Fitzpatrick skin type V; lay reviewers estimated Monk skin tone scale 8 (US pool) or 7 (India pool). This image was taken at an angle: 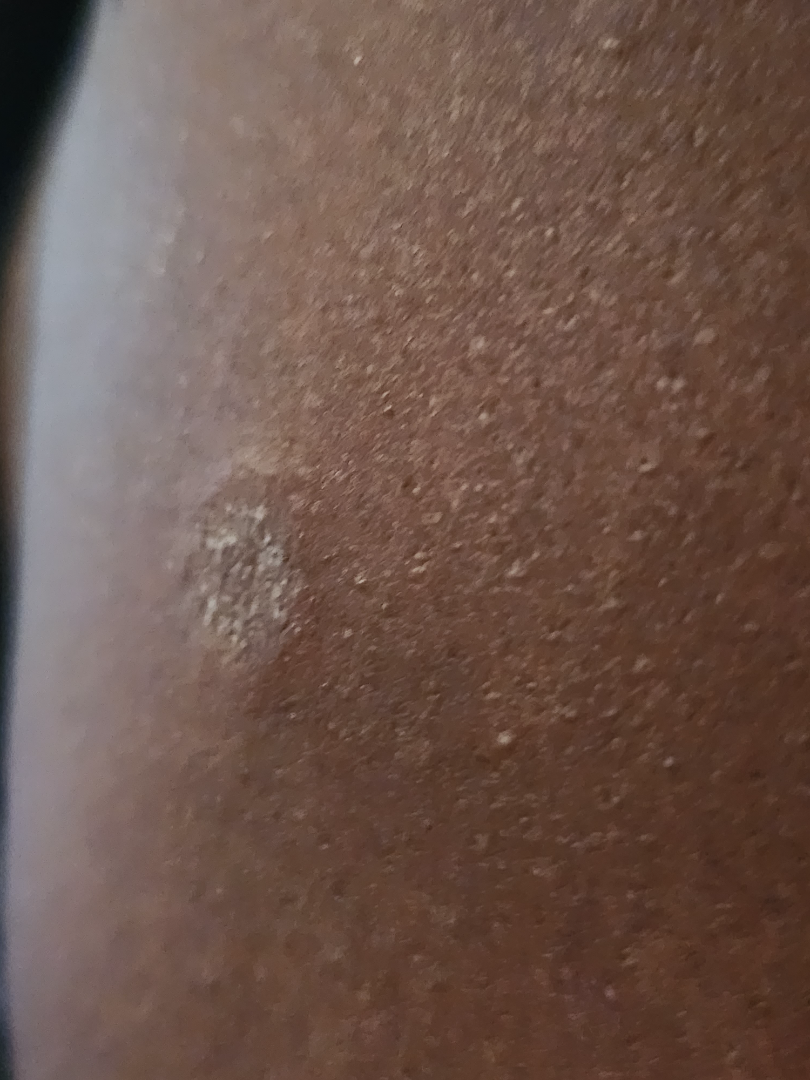The reviewing dermatologist's impression was: the differential, in no particular order, includes Fungal dermatosis and SCC/SCCIS.